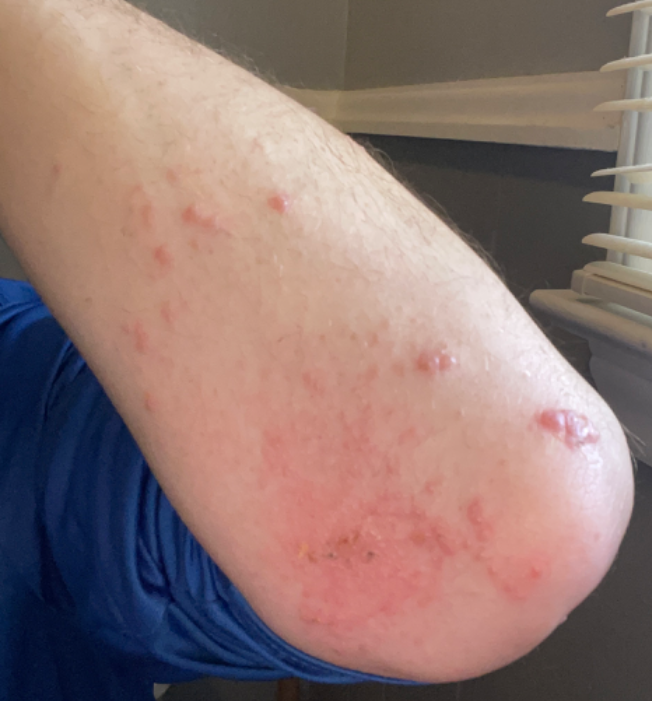assessment: indeterminate from the photograph.